The subject is a female about 30 years old, this is a dermoscopic photograph of a skin lesion: 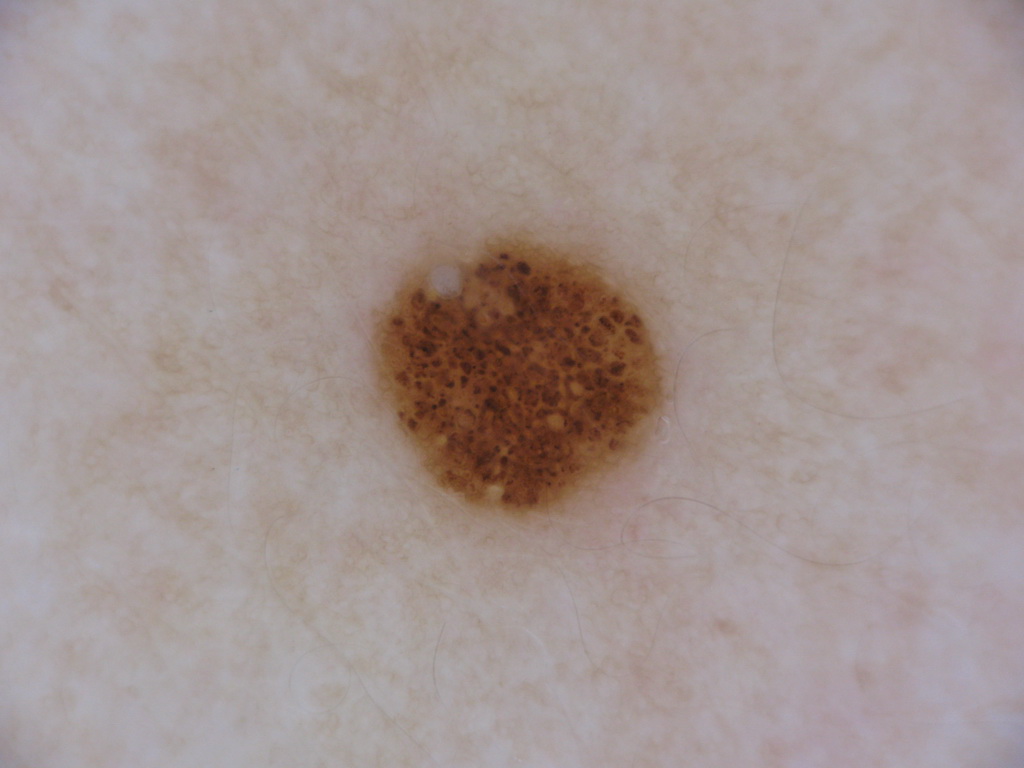Image and clinical context:
The visible lesion spans [368, 225, 665, 519]. On dermoscopy, the lesion shows pigment network and globules. The lesion takes up about 8% of the image.
Impression:
Clinically diagnosed as a melanocytic nevus, a benign lesion.